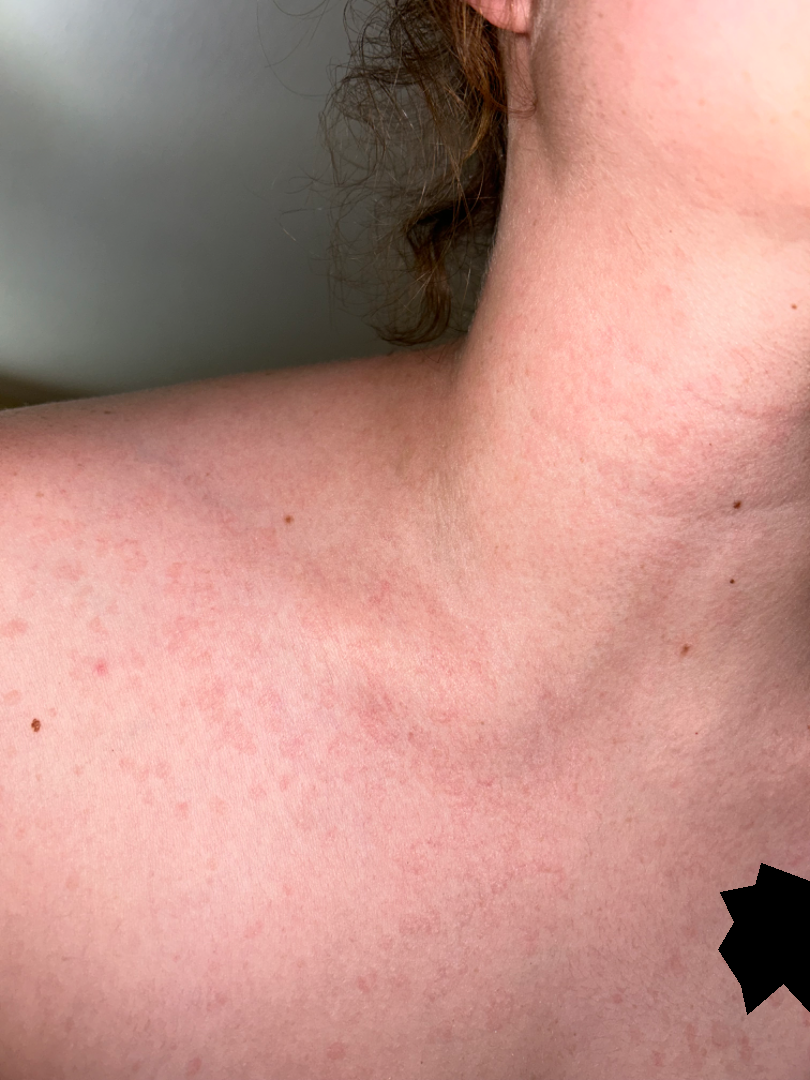On remote dermatologist review, Contact dermatitis and Tinea Versicolor were considered with similar weight; a remote consideration is Pityriasis rosea; less likely is Drug Rash.